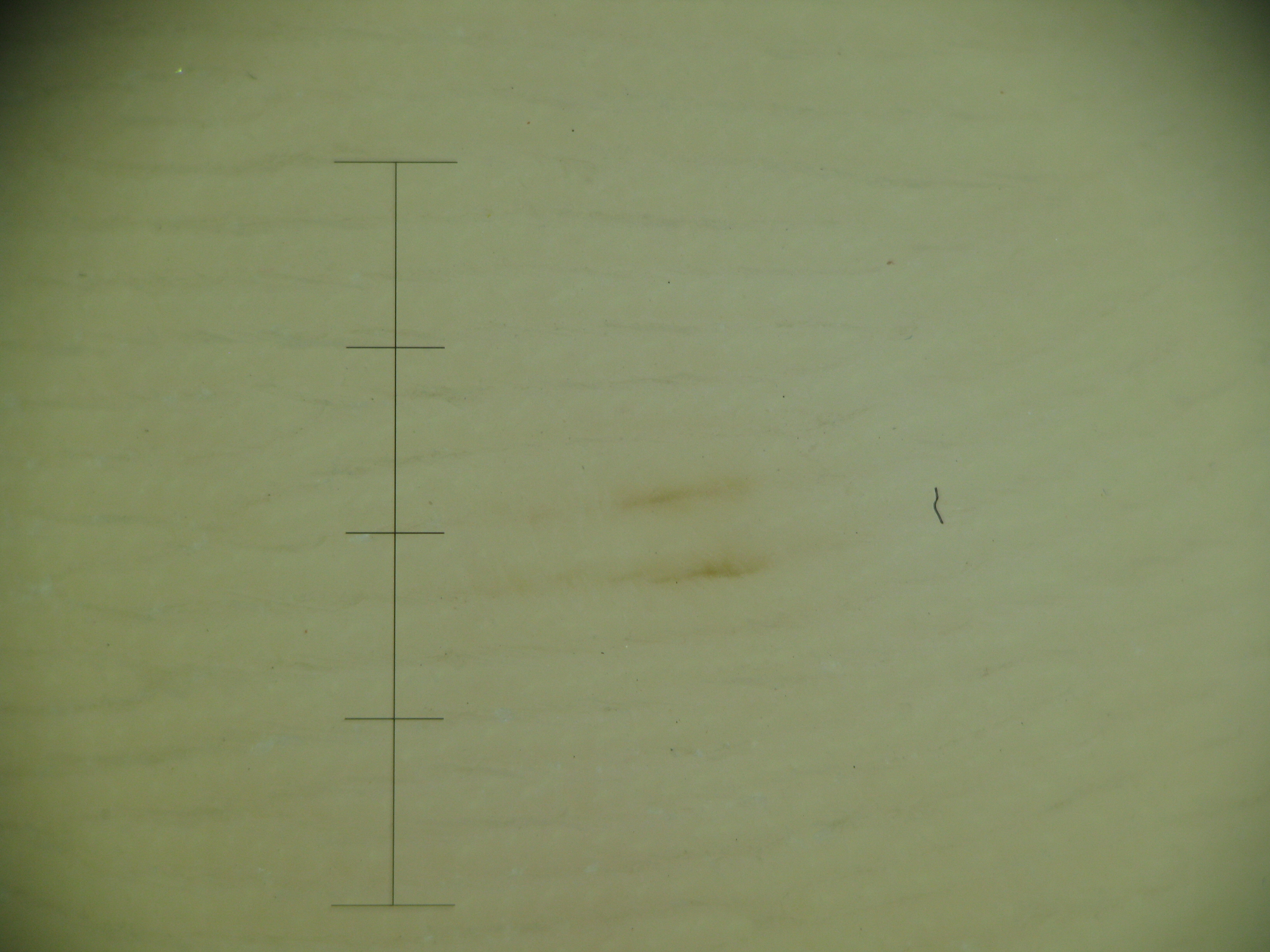Impression:
The diagnostic label was an acral junctional nevus.